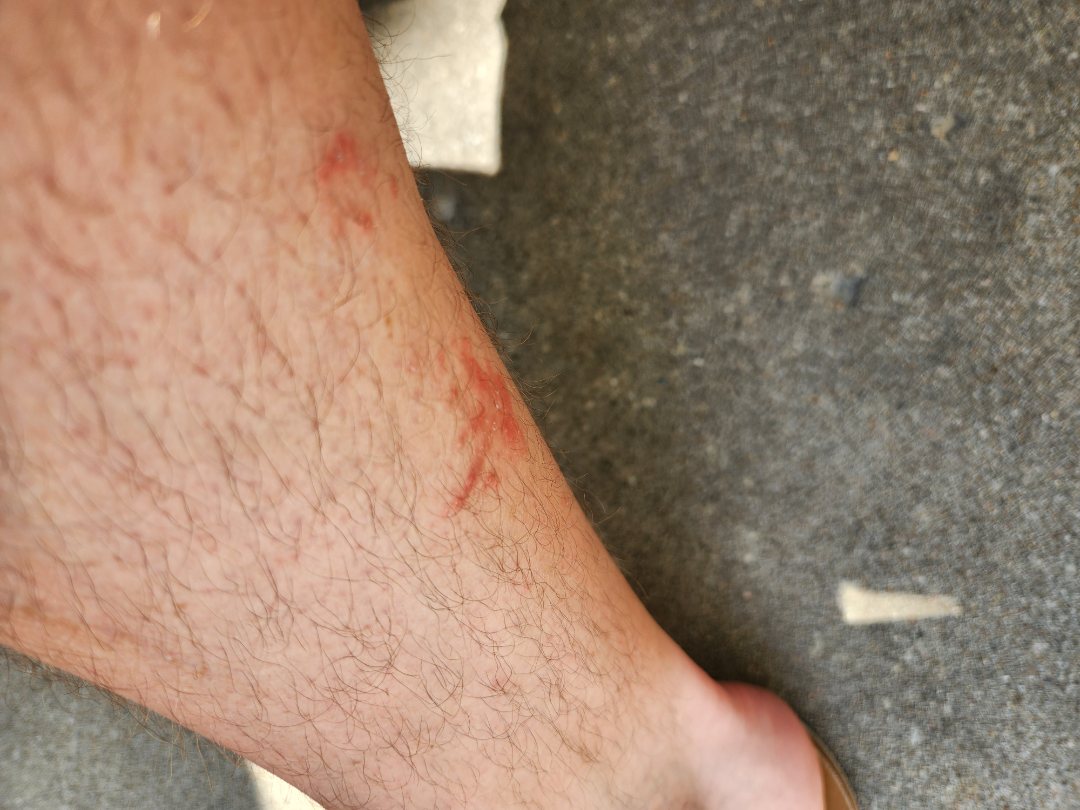| feature | finding |
|---|---|
| assessment | not assessable |